The photo was captured at an angle; located on the head or neck — 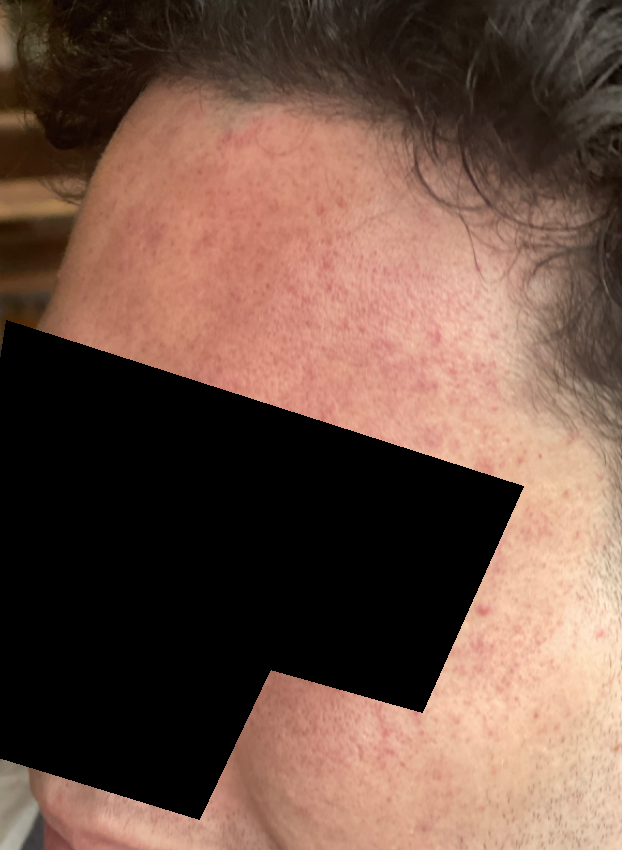history=about one day | other reported symptoms=none reported | patient-reported symptoms=bothersome appearance | surface texture=flat | assessment=three dermatologists independently reviewed the case: most likely Rosacea; also consider Acne.